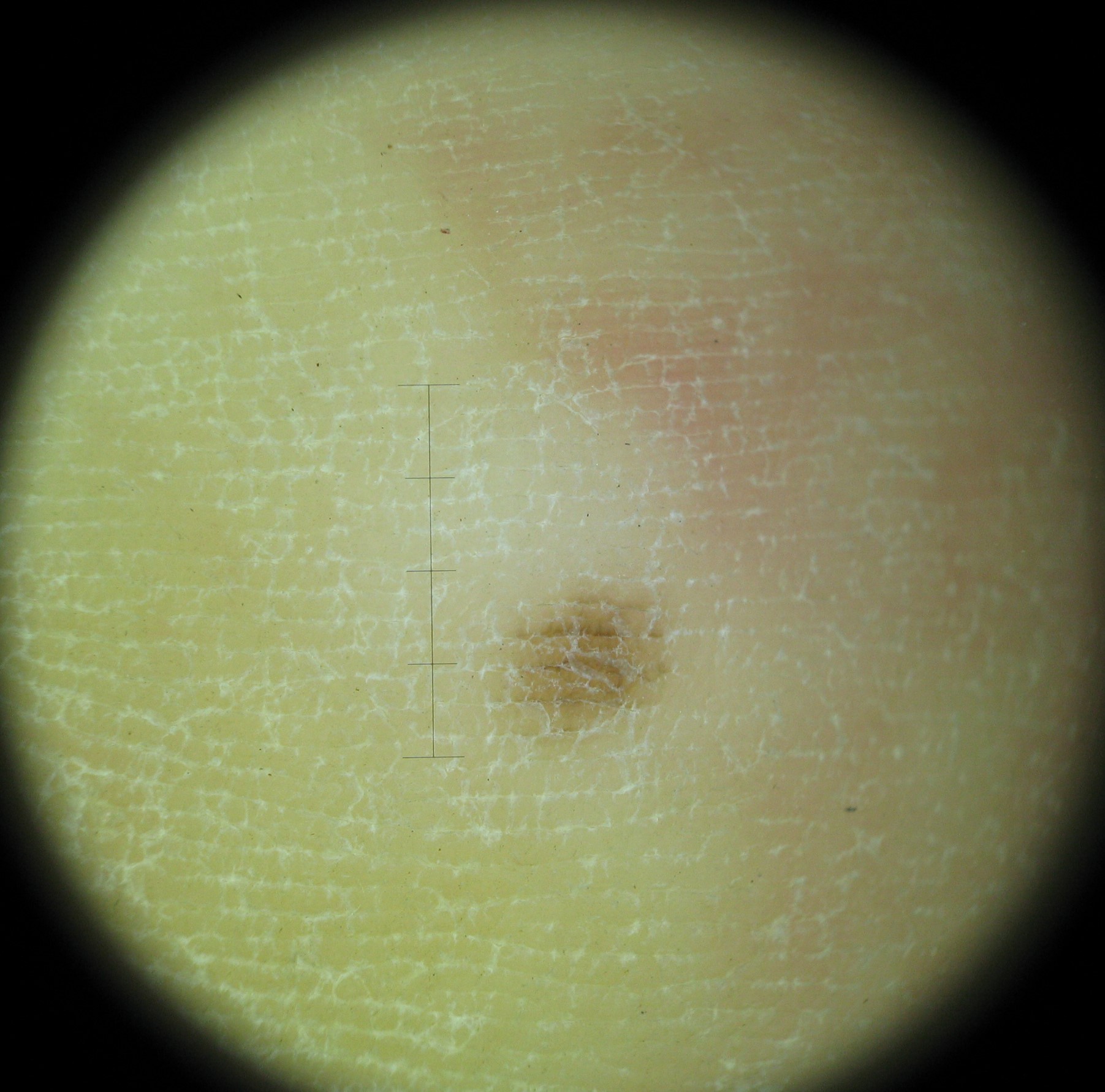Labeled as an acral junctional nevus.